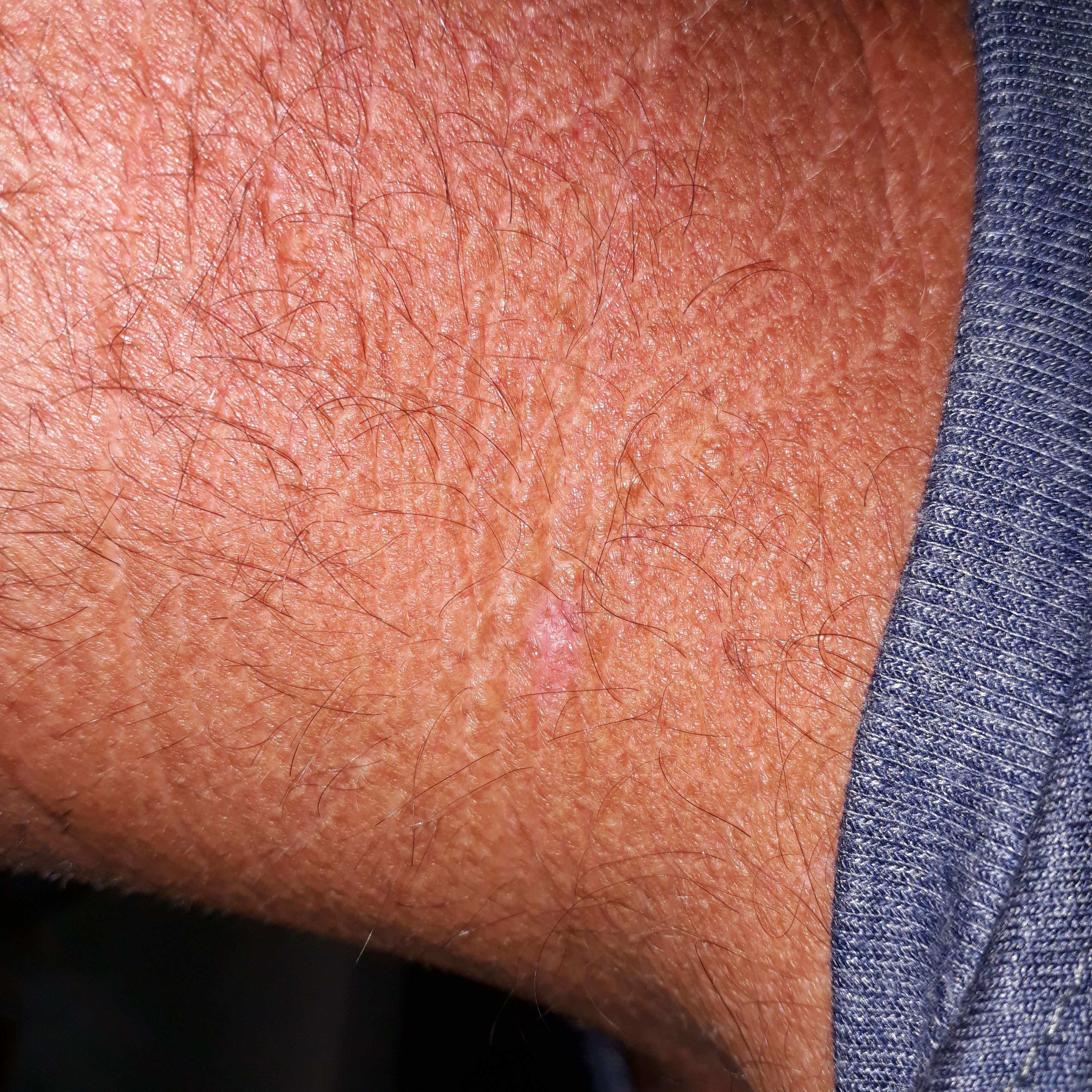| key | value |
|---|---|
| patient | 45 years of age |
| image | clinical photograph |
| reported symptoms | itching, elevation |
| diagnostic label | actinic keratosis (clinical consensus) |